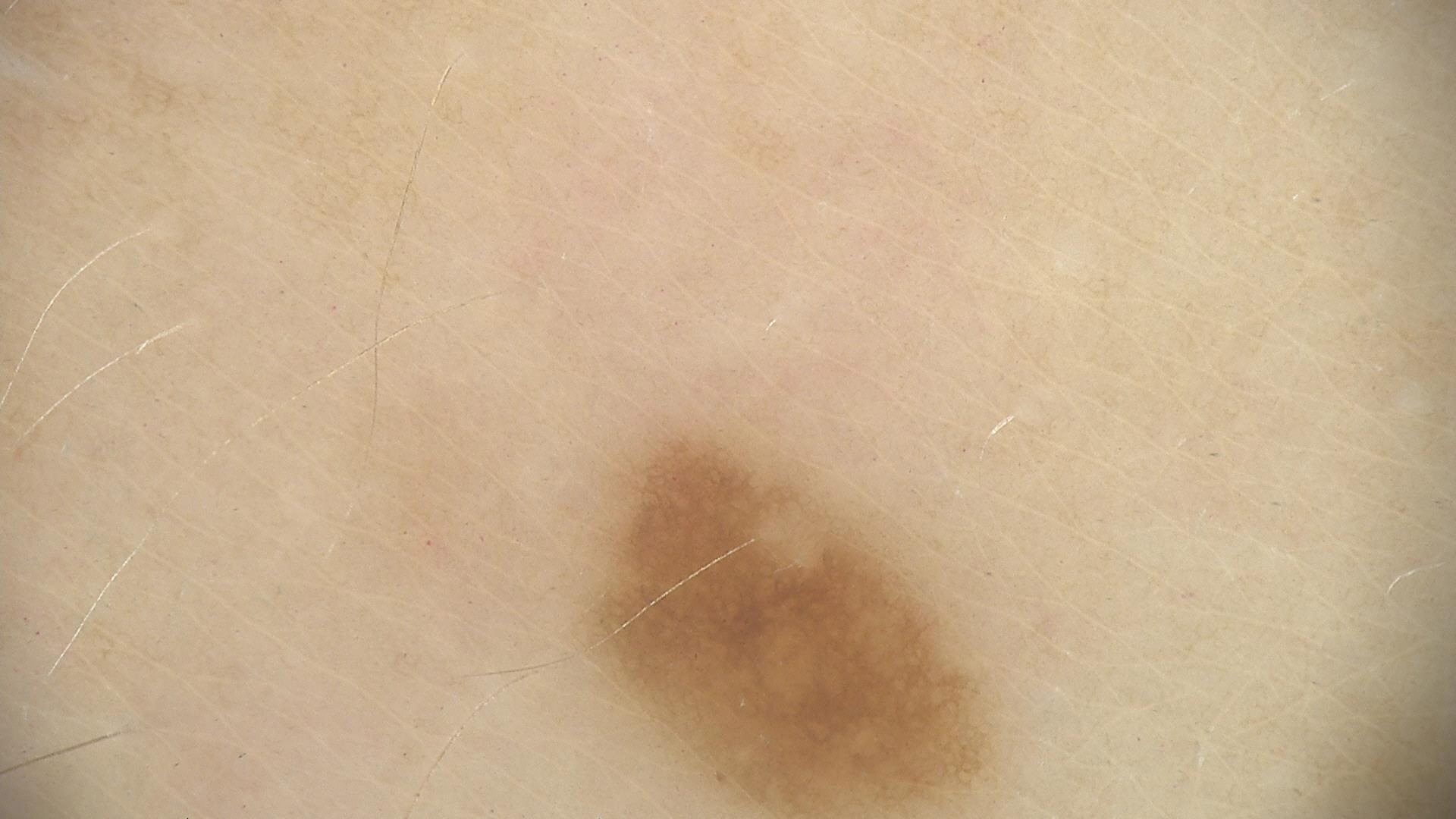A dermoscopic photograph of a skin lesion. Classified as a banal lesion — a junctional nevus.